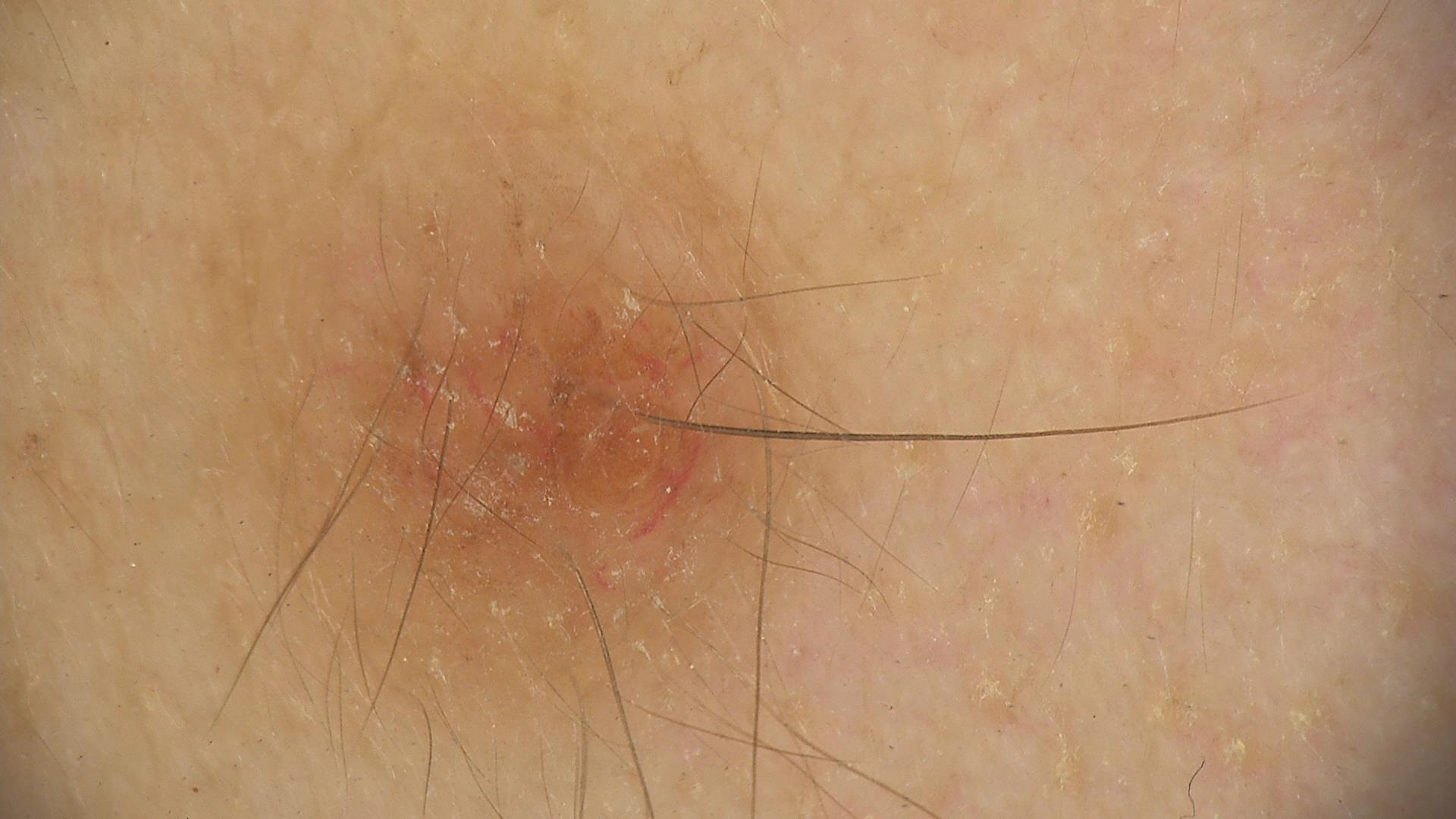The diagnosis was a banal lesion — a dermal nevus.